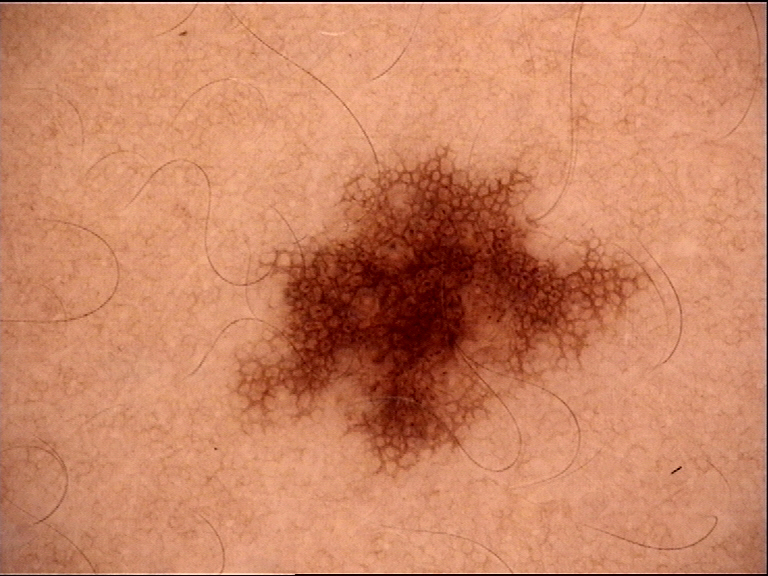assessment — dysplastic junctional nevus (expert consensus).